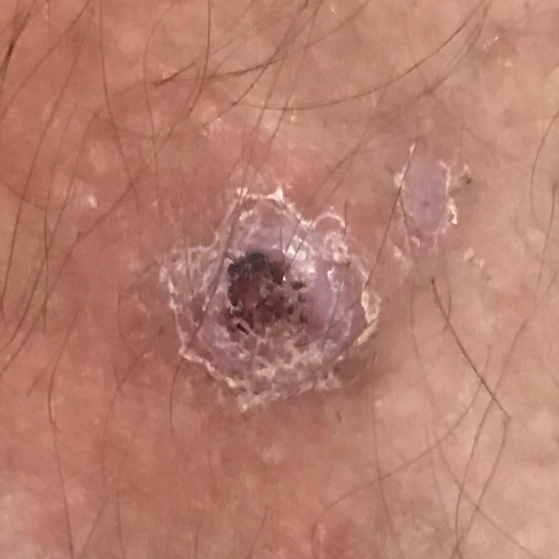patient — male, 69 years old; Fitzpatrick — II; image type — clinical photo; body site — a thigh; lesion size — 12x7 mm; patient-reported symptoms — elevation / no pain; diagnosis — squamous cell carcinoma (biopsy-proven).